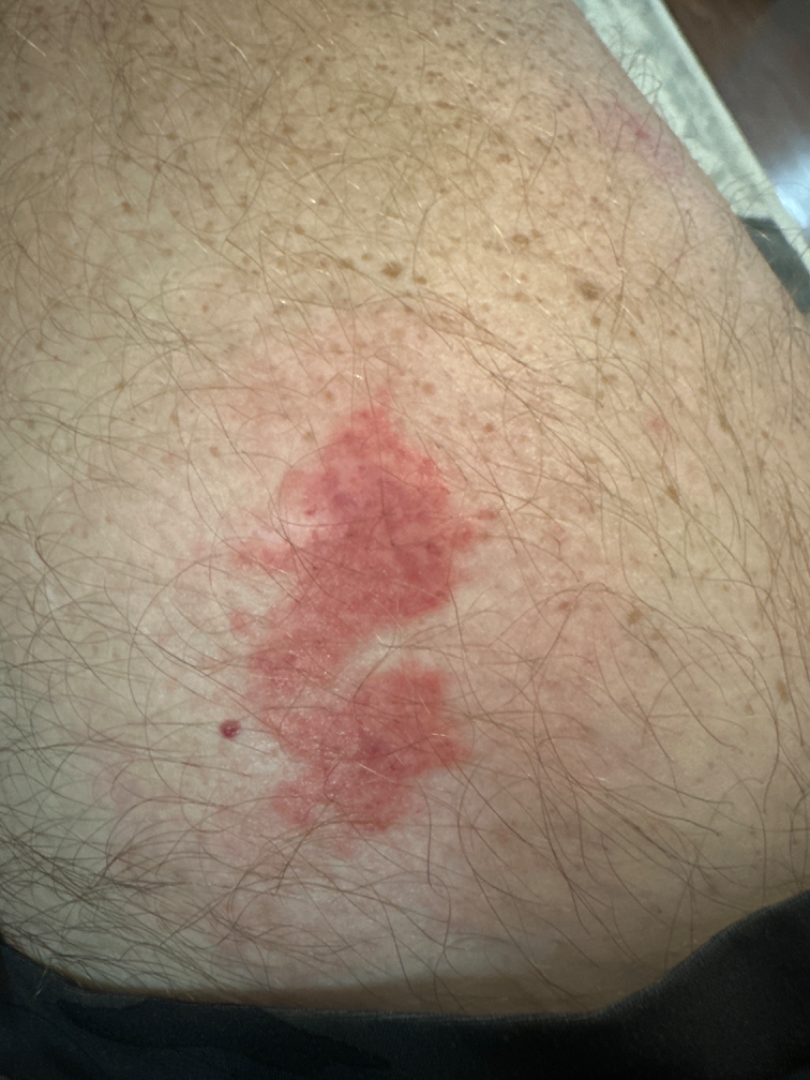- location: leg
- duration: less than one week
- reported symptoms: itching
- patient: male, age 40–49
- patient's own categorization: a rash
- skin tone: Fitzpatrick phototype II; lay graders estimated MST 2 (US pool) or 4 (India pool)
- view: close-up
- dermatologist impression: Inflammatory dermatosis and SCC/SCCIS were each considered, in no particular order; less probable is Skin and soft tissue atypical mycobacterial infection